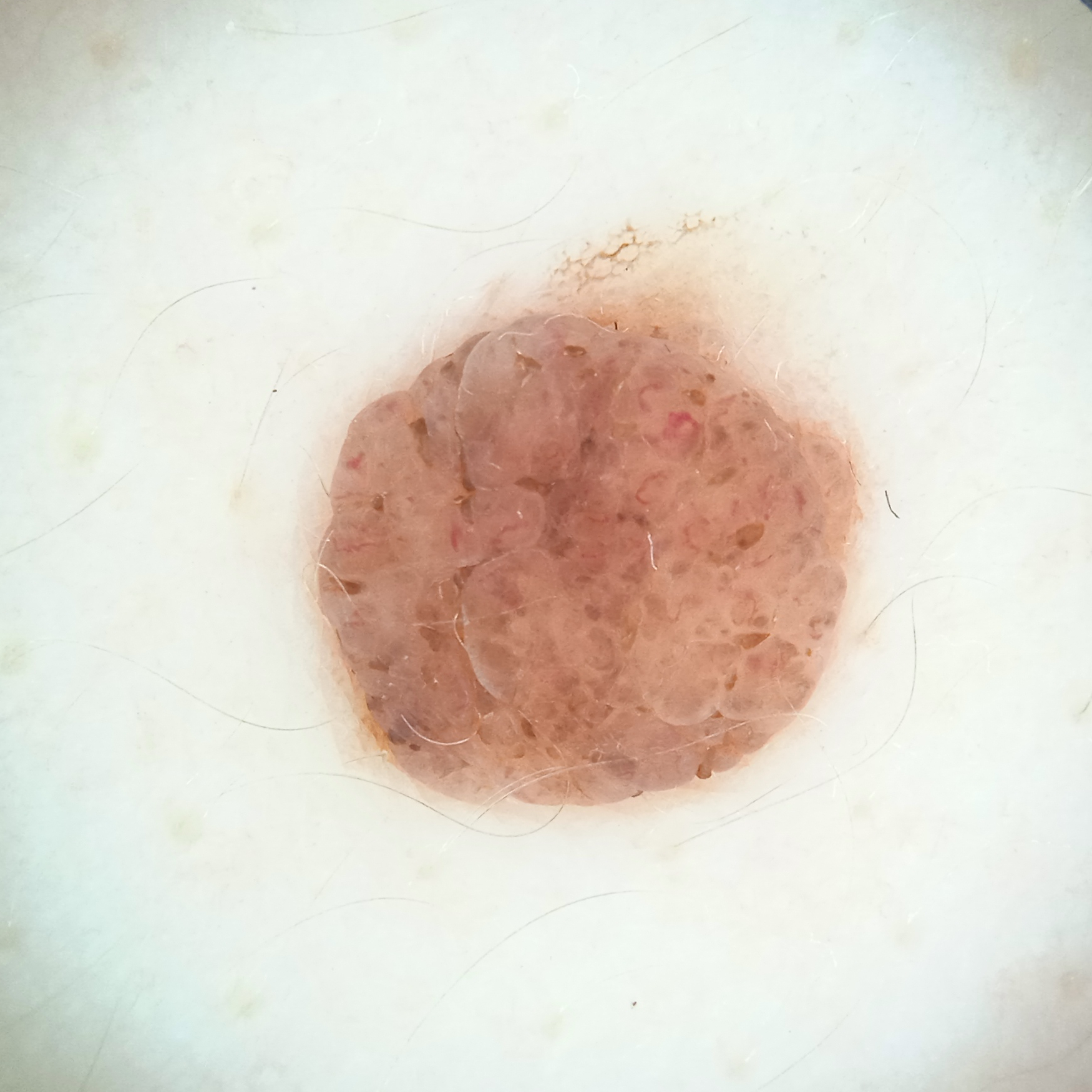<skin_lesion>
  <sun_reaction>skin reddens with sun exposure</sun_reaction>
  <image>dermoscopic image</image>
  <risk_factors>
    <positive>a history of sunbed use</positive>
    <negative>no prior organ transplant</negative>
  </risk_factors>
  <lesion_location>the back</lesion_location>
  <lesion_size>
    <diameter_mm>5.6</diameter_mm>
  </lesion_size>
  <diagnosis>
    <name>melanocytic nevus</name>
    <malignancy>benign</malignancy>
  </diagnosis>
</skin_lesion>